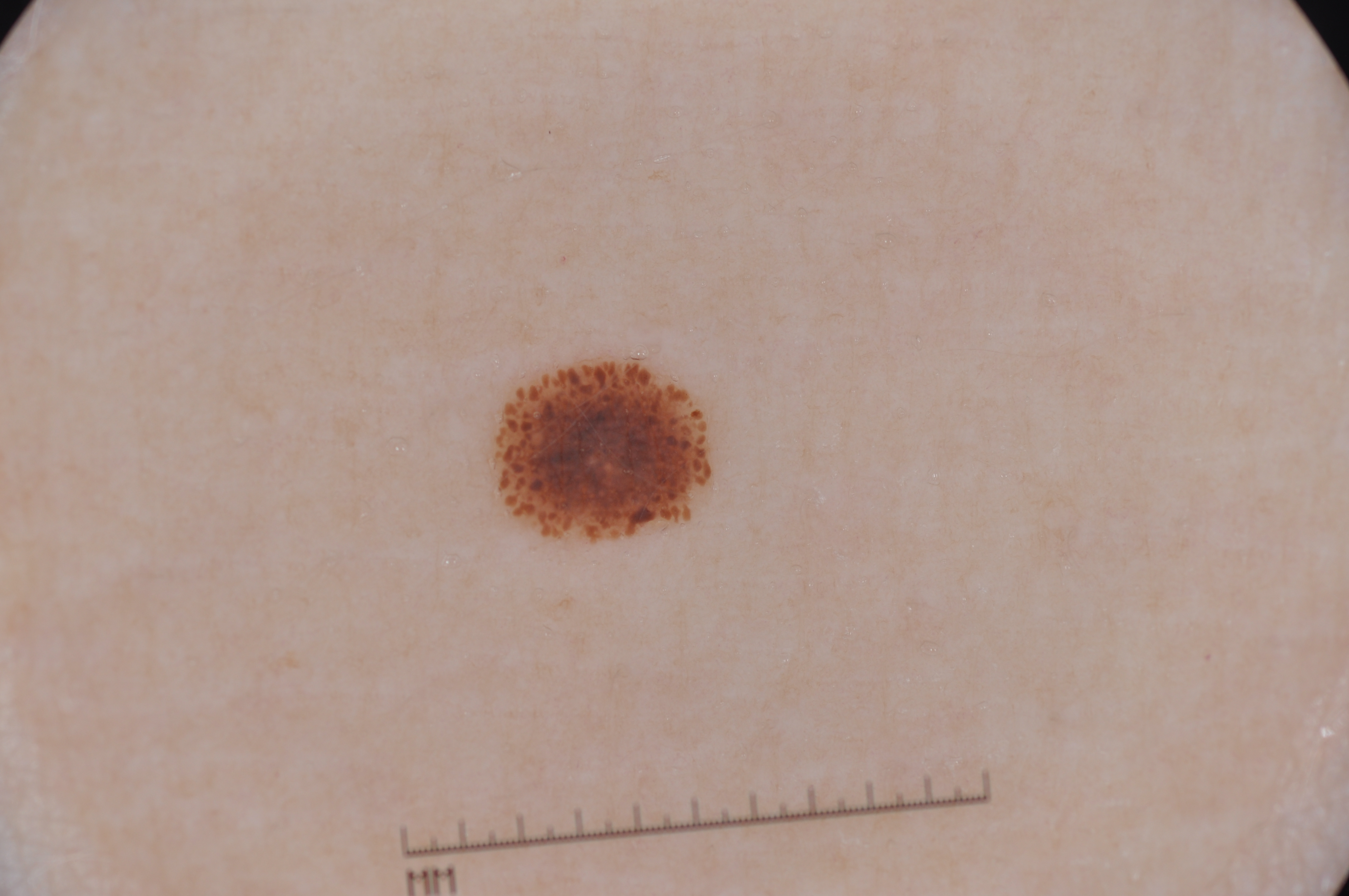Q: Patient demographics?
A: female, about 40 years old
Q: What is the imaging modality?
A: dermatoscopic image of a skin lesion
Q: Where is the lesion located?
A: x1=485 y1=352 x2=718 y2=546
Q: What dermoscopic features are not present?
A: negative network, streaks, milia-like cysts, and pigment network
Q: Lesion extent?
A: small
Q: What is this lesion?
A: a melanocytic nevus